A female patient, roughly 35 years of age; a dermoscopy image of a single skin lesion: 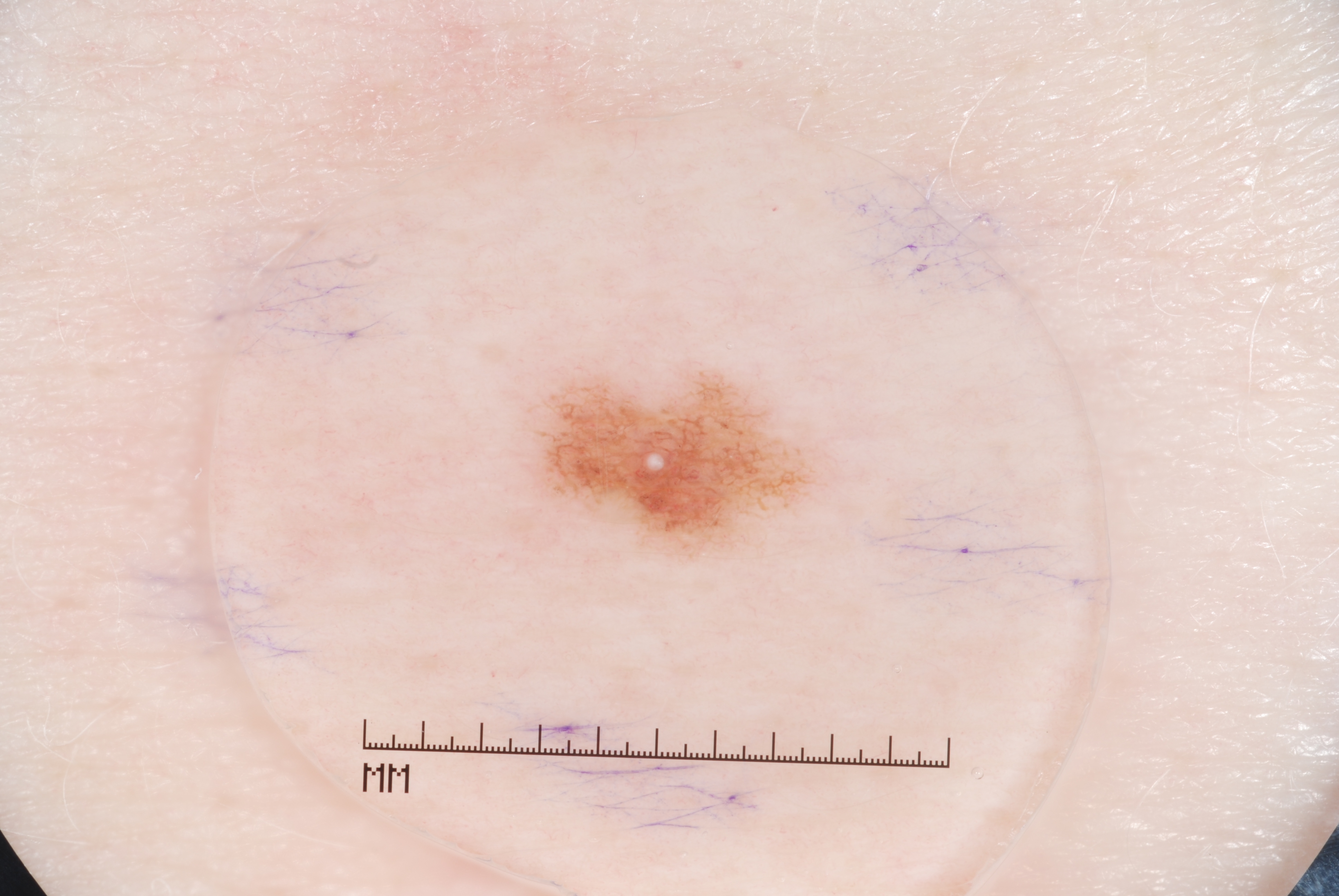{
  "lesion_location": {
    "bbox_xyxy": [
      514,
      362,
      828,
      565
    ]
  },
  "lesion_extent": "small",
  "dermoscopic_features": {
    "present": [
      "milia-like cysts",
      "pigment network"
    ],
    "absent": [
      "streaks",
      "negative network"
    ]
  },
  "diagnosis": {
    "name": "melanocytic nevus",
    "malignancy": "benign",
    "lineage": "melanocytic",
    "provenance": "clinical"
  }
}